Present for one to three months · FST III · texture is reported as rough or flaky · the patient also reports joint pain · female contributor, age 50–59 · the arm and leg are involved · this is a close-up image · reported lesion symptoms include itching — 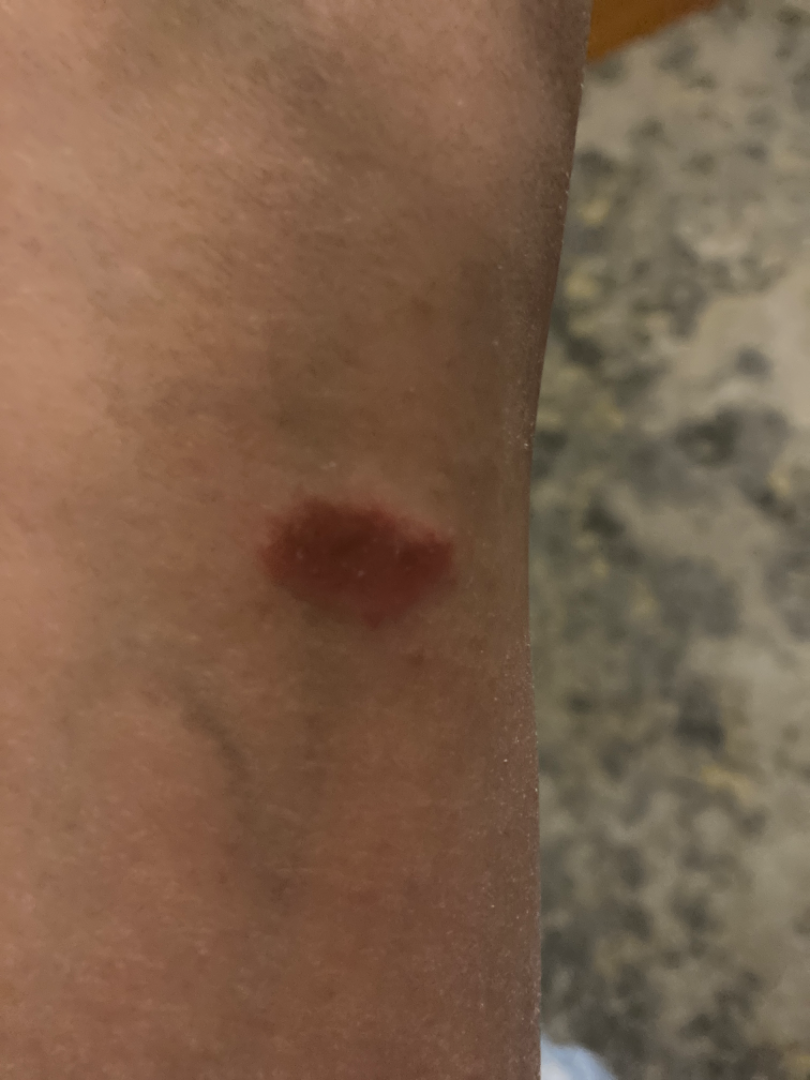On dermatologist assessment of the image: most consistent with Eczema.